A skin lesion imaged with a dermatoscope.
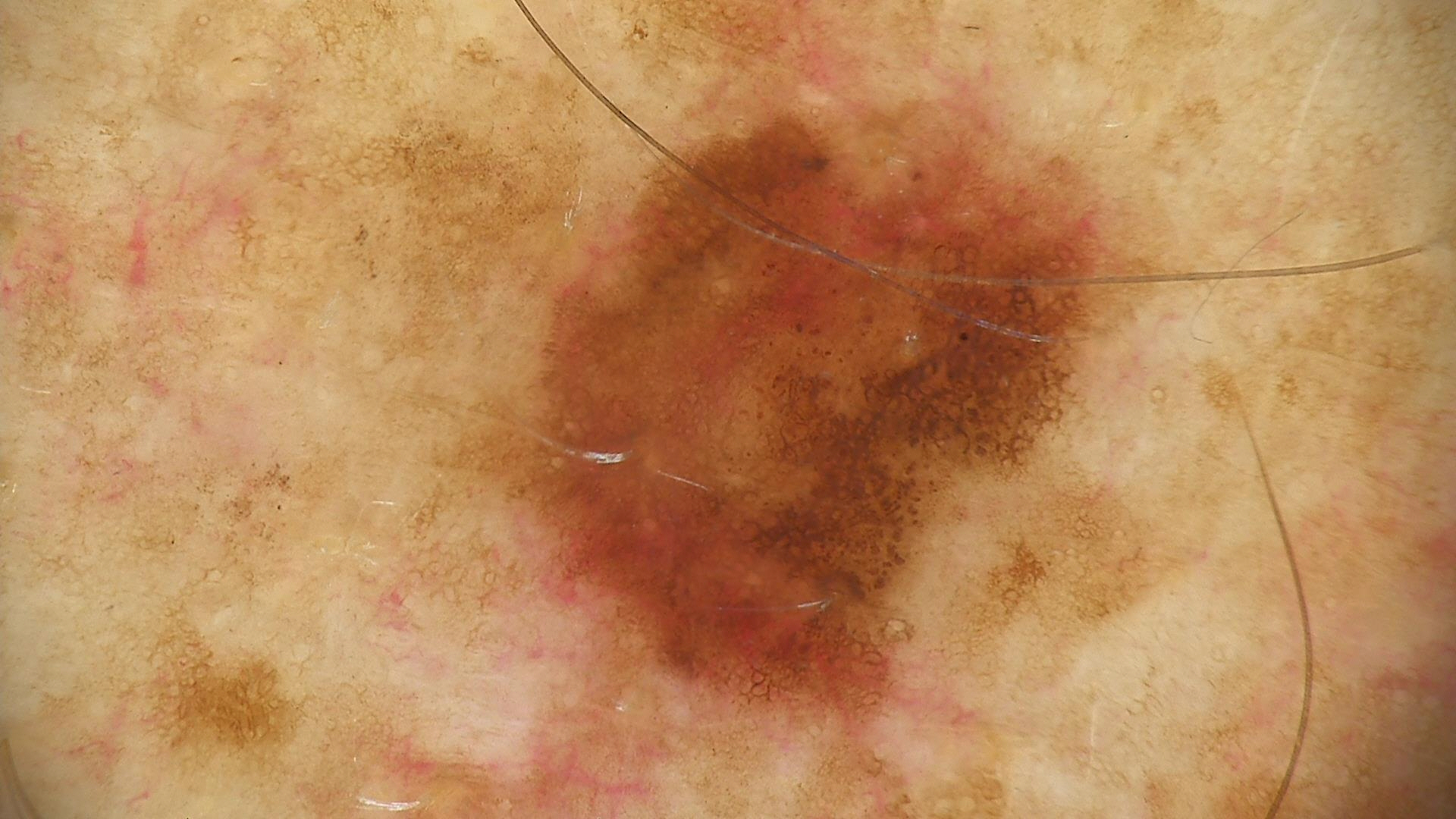assessment=dysplastic junctional nevus (expert consensus).